A dermatoscopic image of a skin lesion.
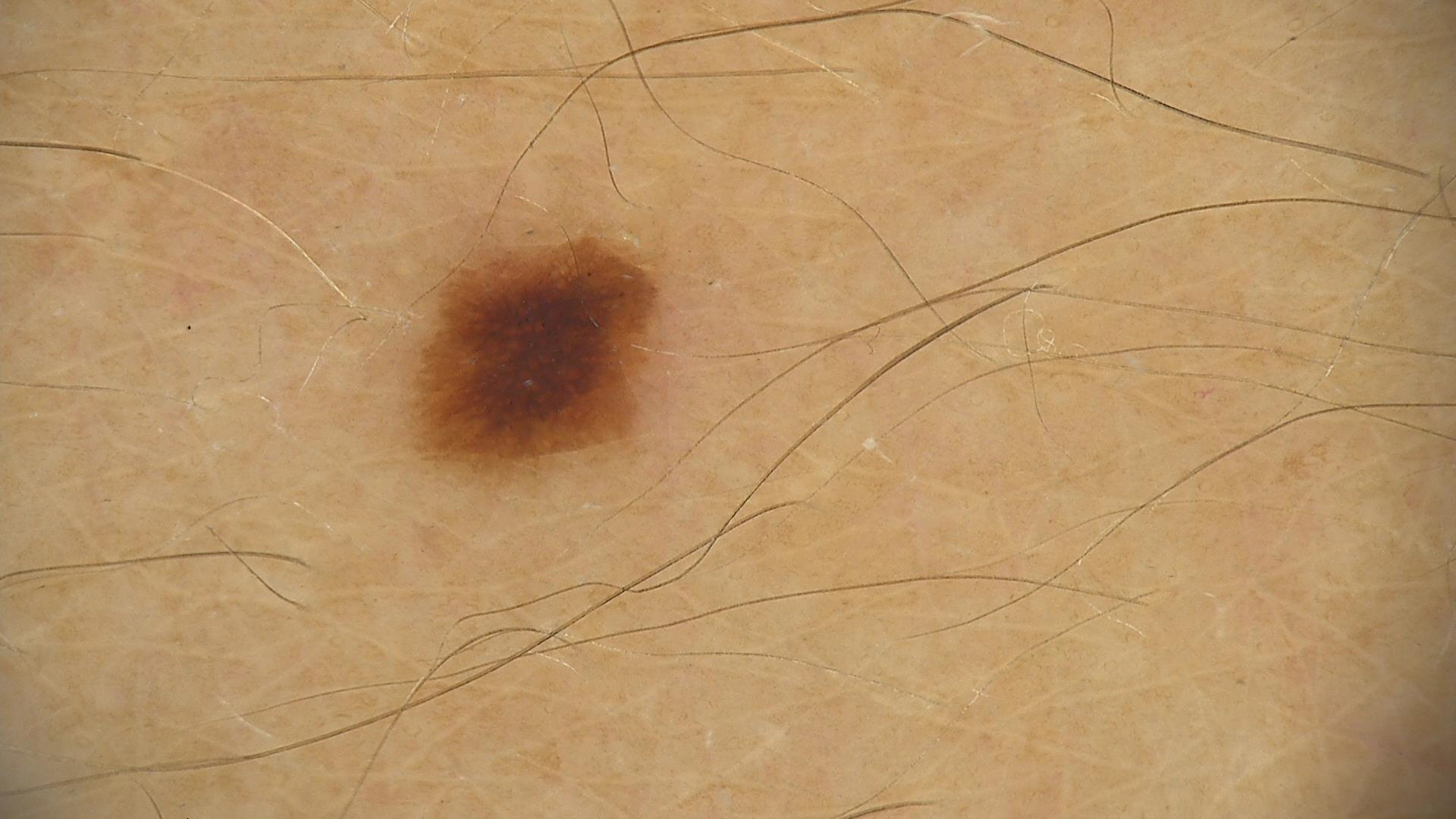Impression:
The diagnostic label was a dysplastic junctional nevus.